A skin lesion imaged with a dermatoscope.
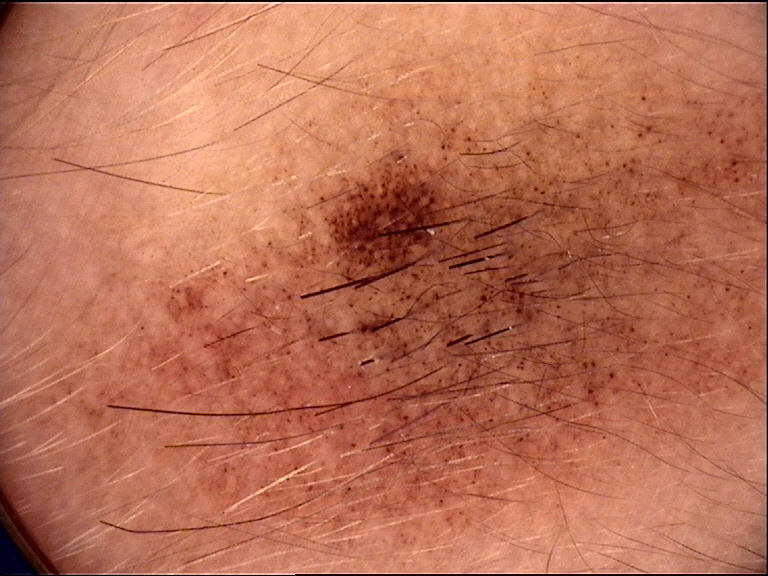Summary: The morphology is that of a banal lesion. Conclusion: Classified as a congenital junctional nevus.